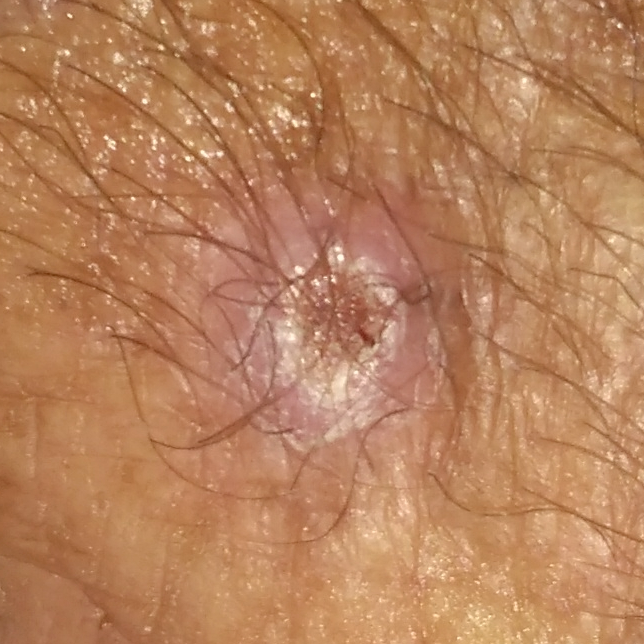FST: III | patient: male, aged 62 | exposures: pesticide exposure, prior skin cancer (patient or family) | modality: clinical photograph | anatomic site: a hand | lesion diameter: 10 × 9 mm | symptoms: itching, elevation, growth, bleeding / no change in appearance | pathology: basal cell carcinoma (biopsy-proven).